A dermoscopy image of a skin lesion. The patient says their skin reddens with sun exposure. A male patient 83 years old — 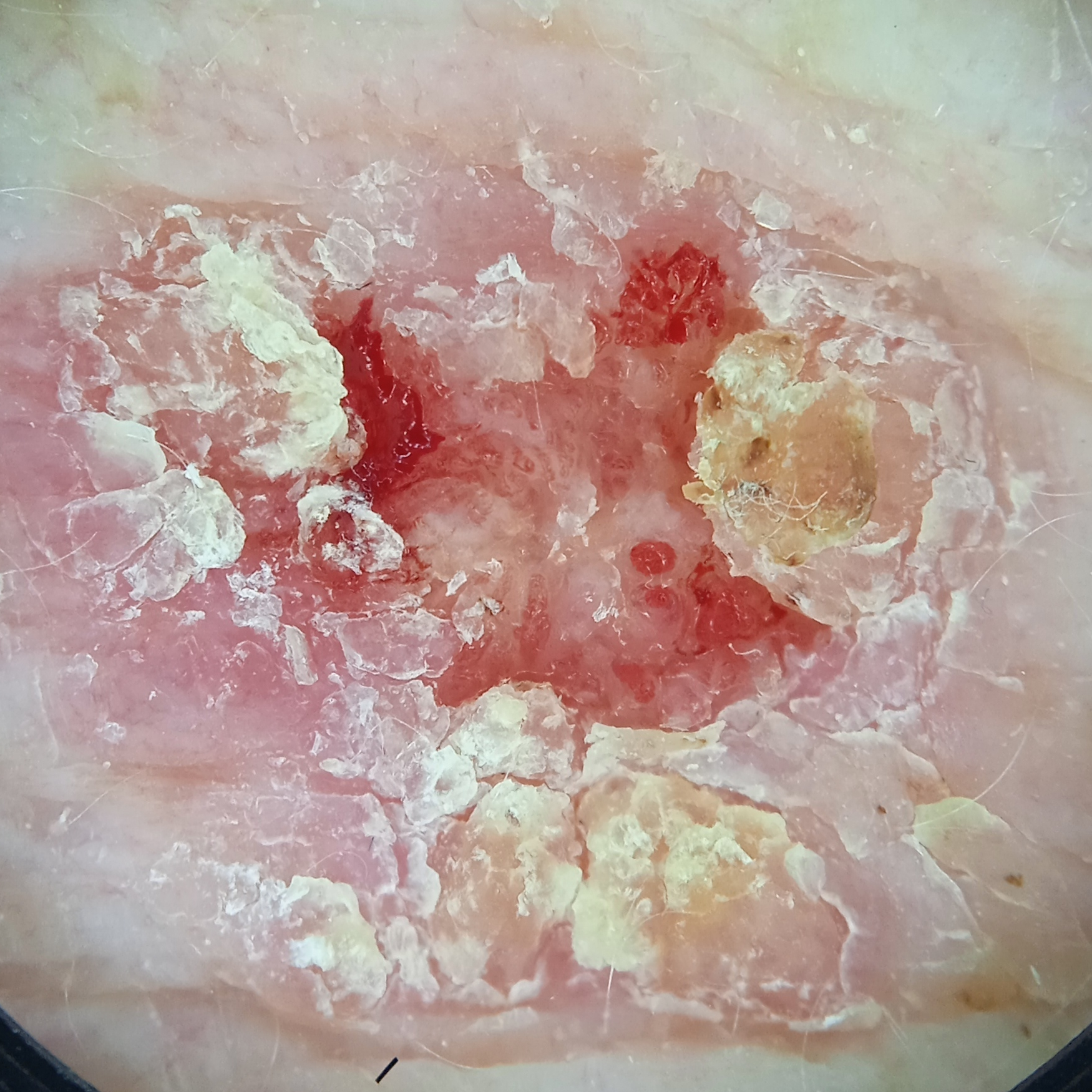The lesion is on the torso. Measuring roughly 14.5 mm. The lesion was assessed as a squamous cell carcinoma.